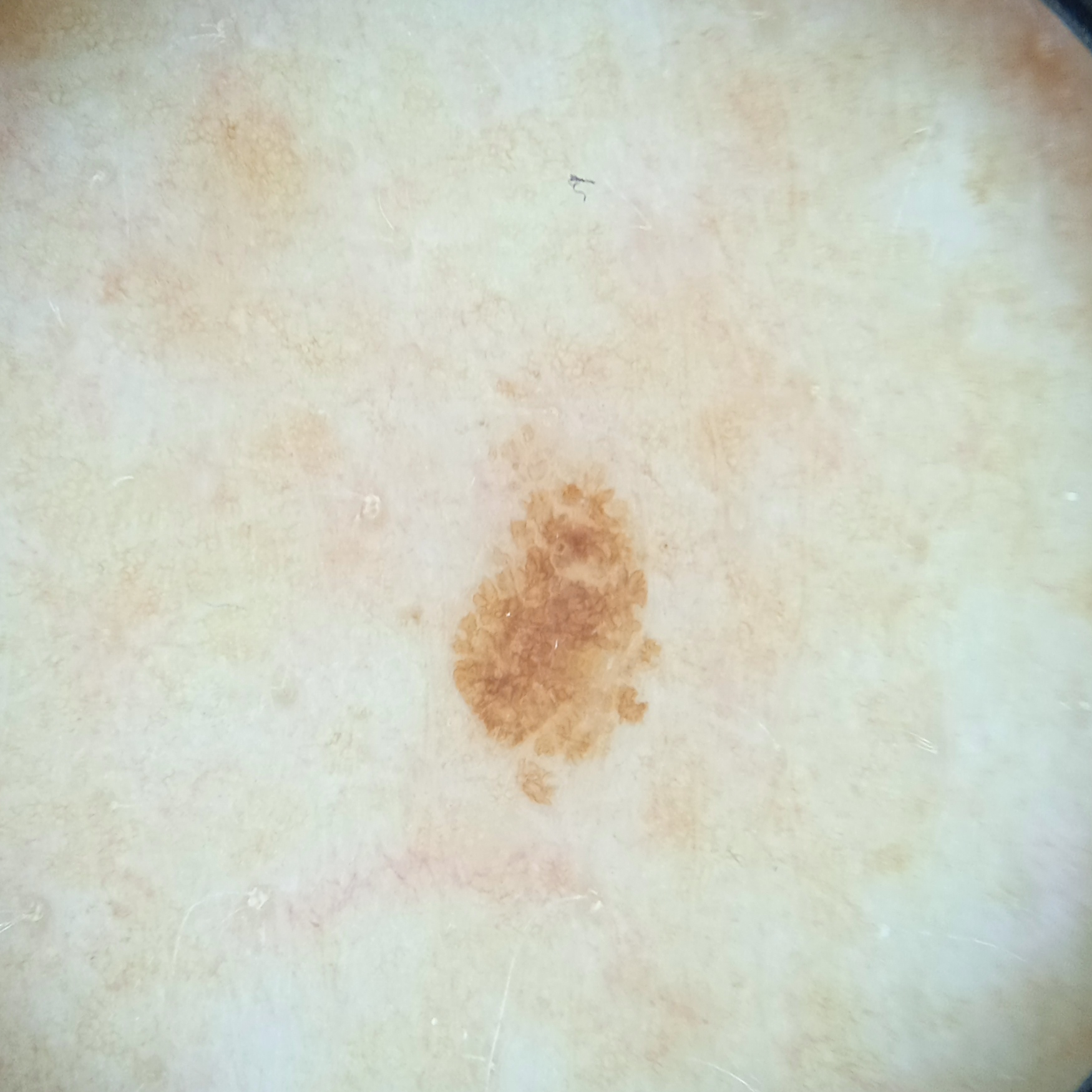Clinical context:
Collected as part of a research study, without a referral diagnosis. The patient says their skin reddens with sun exposure. A female subject 73 years old. A dermoscopic image of a skin lesion. The patient describes having few moles overall. The lesion is located on the back.
Conclusion:
The dermatologists' assessment was a seborrheic keratosis.